A dermatoscopic image of a skin lesion.
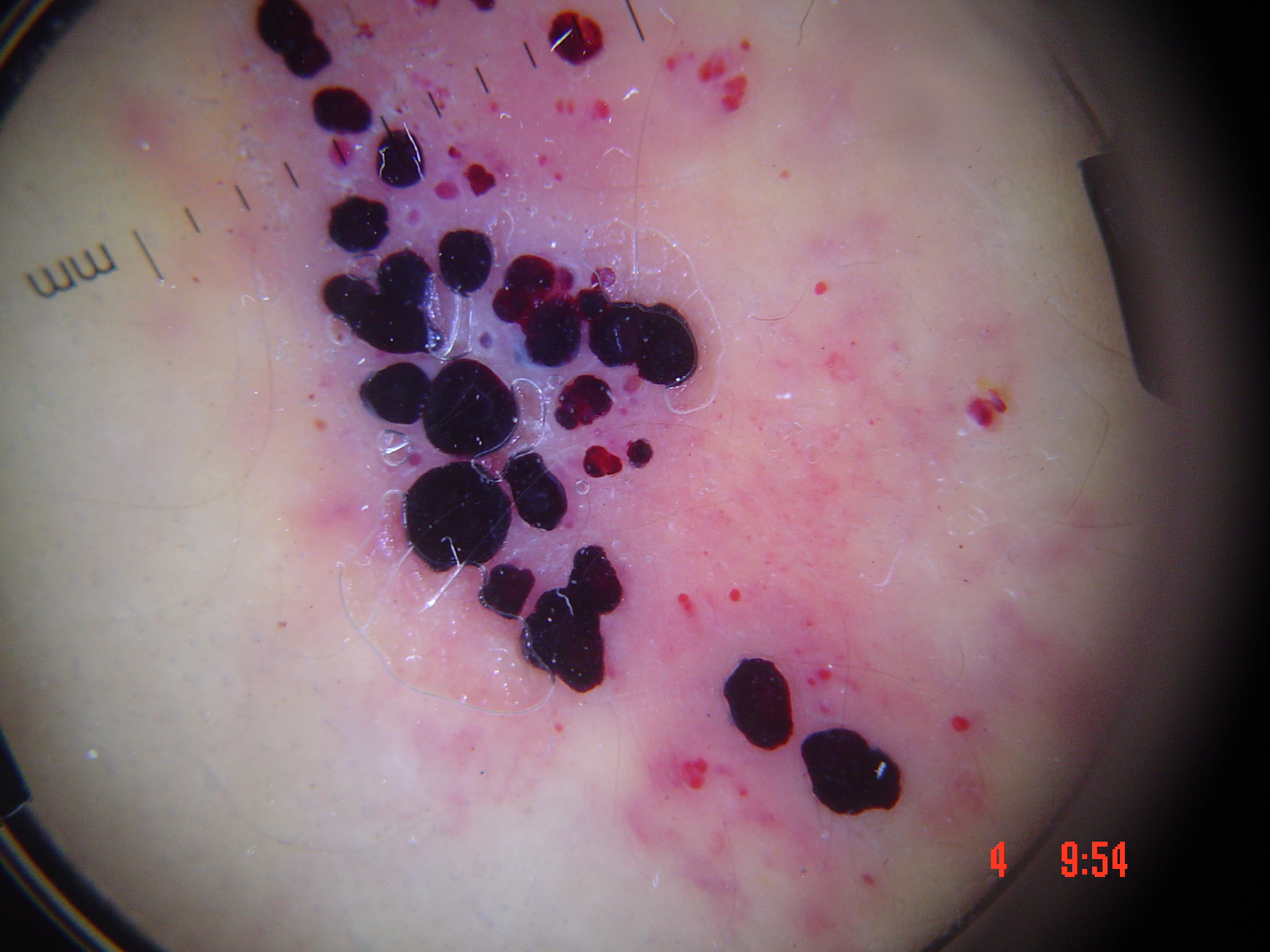Diagnosed as a benign lesion — an angiokeratoma.